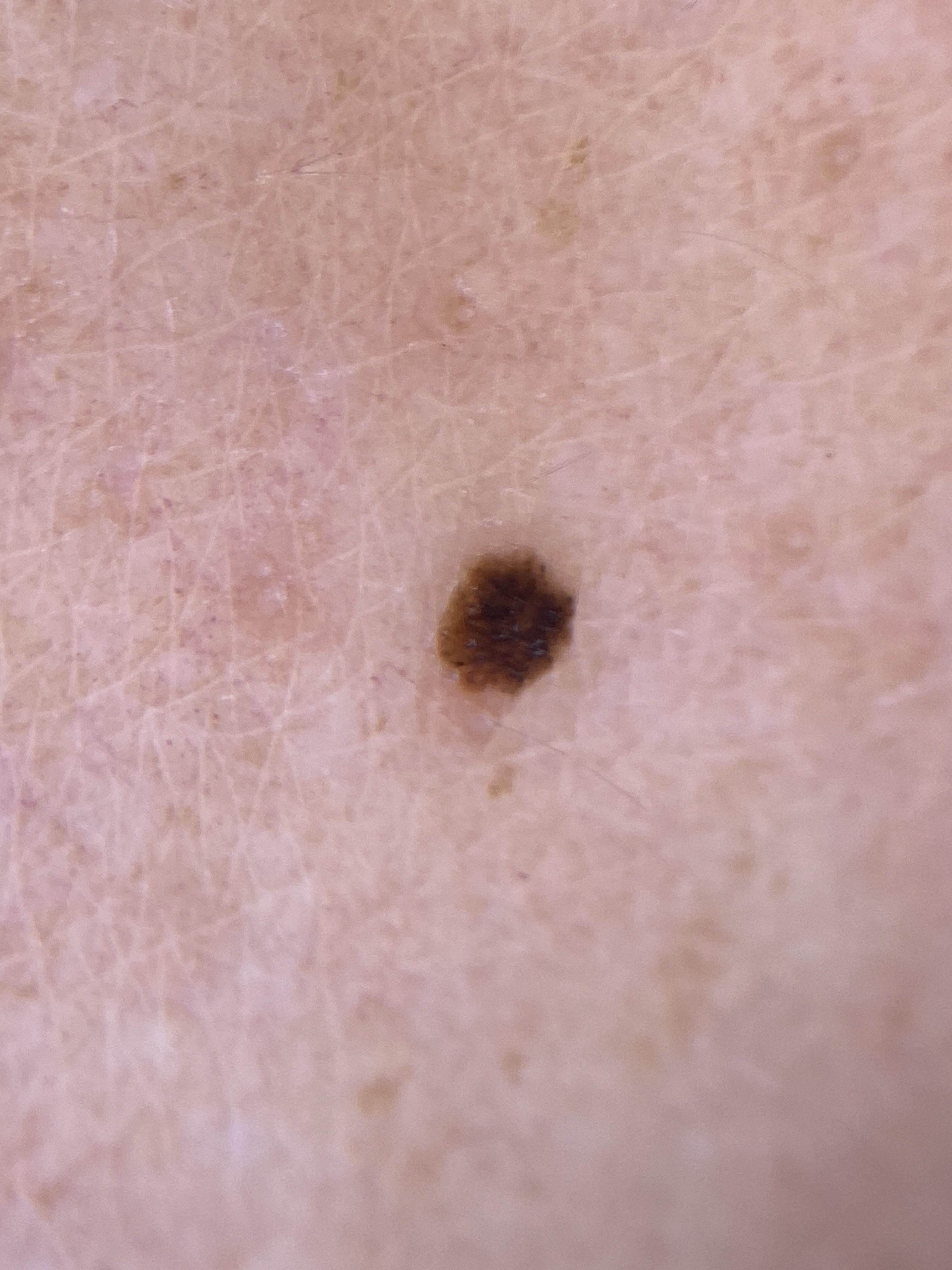The chart documents melanoma in a first-degree relative.
A female subject aged approximately 45.
Dermoscopy of a skin lesion.
The lesion is on an upper extremity.
The clinical impression was a benign, melanocytic lesion — a nevus.